A dermoscopy image of a single skin lesion: 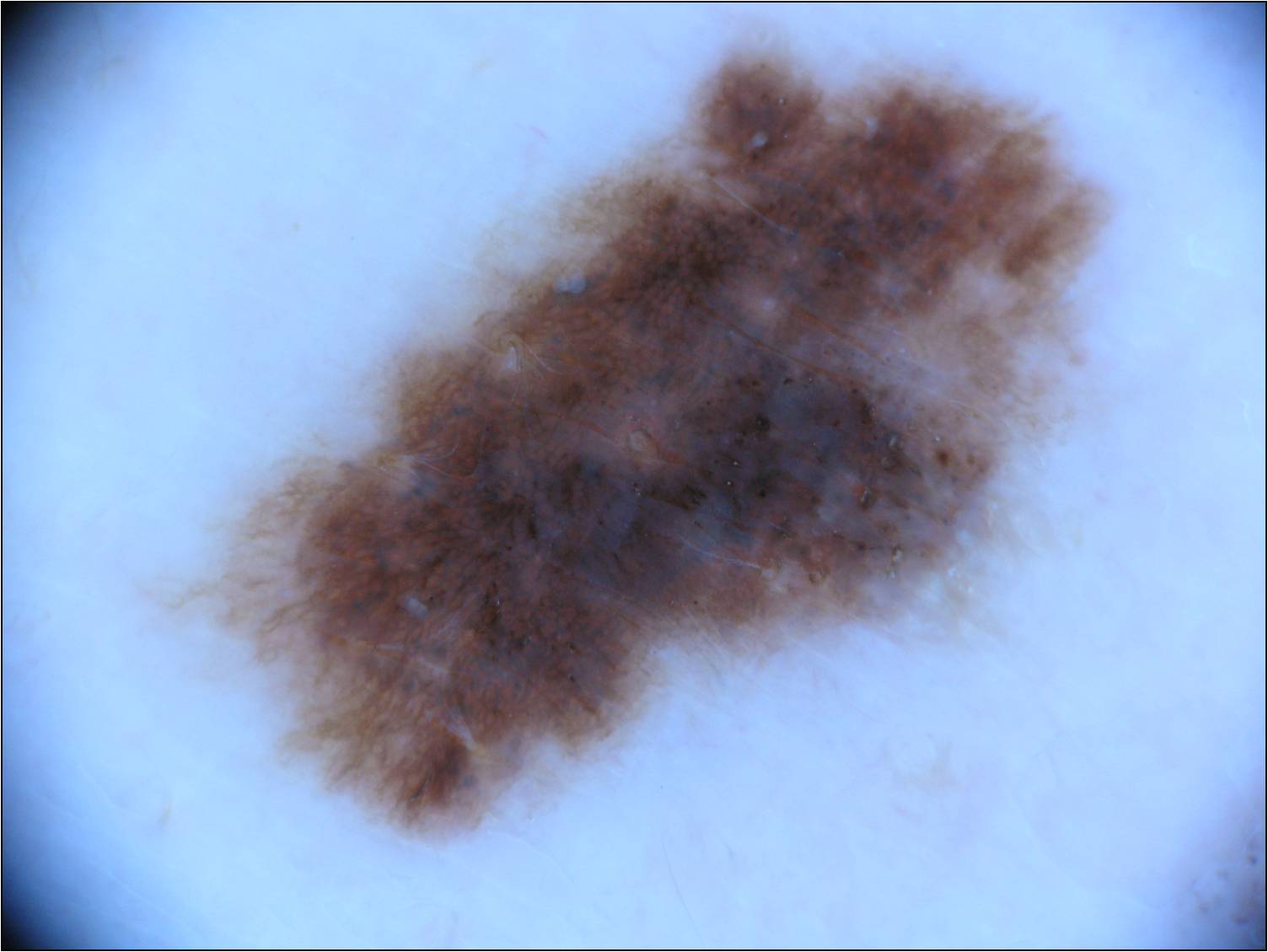{"lesion_location": {"bbox_xyxy": [122, 15, 1151, 857]}, "diagnosis": {"name": "melanocytic nevus", "malignancy": "benign", "lineage": "melanocytic", "provenance": "clinical"}}